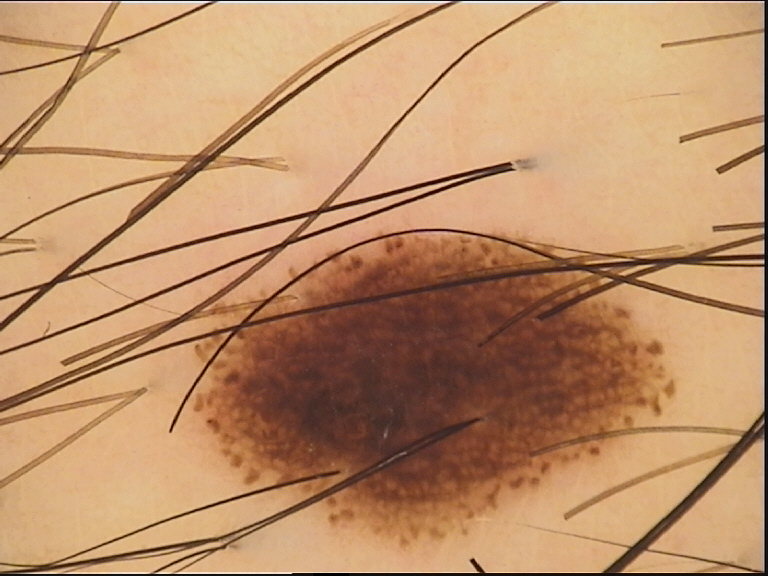Labeled as a dysplastic compound nevus.